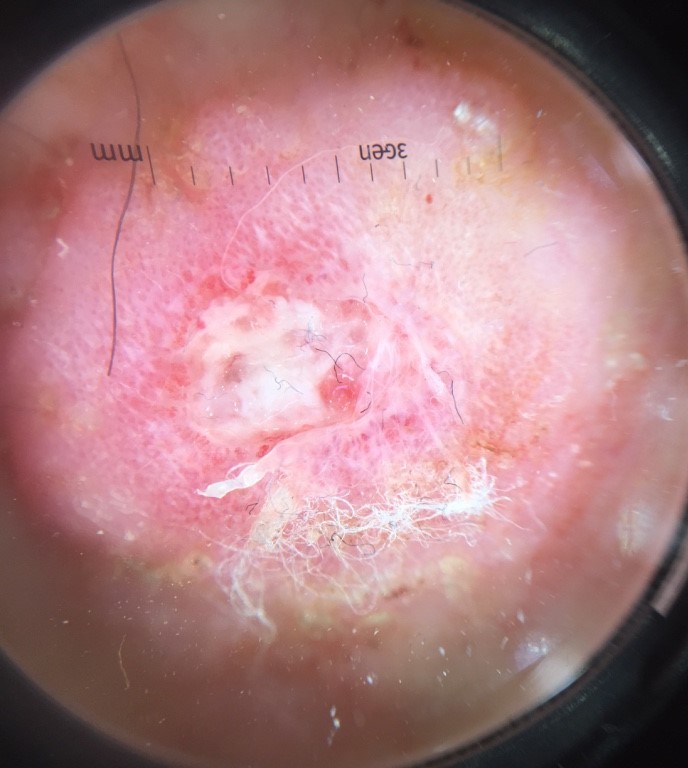<lesion>
<image>dermoscopy</image>
<diagnosis>
<name>squamous cell carcinoma</name>
<code>scc</code>
<malignancy>malignant</malignancy>
<super_class>non-melanocytic</super_class>
<confirmation>histopathology</confirmation>
</diagnosis>
</lesion>